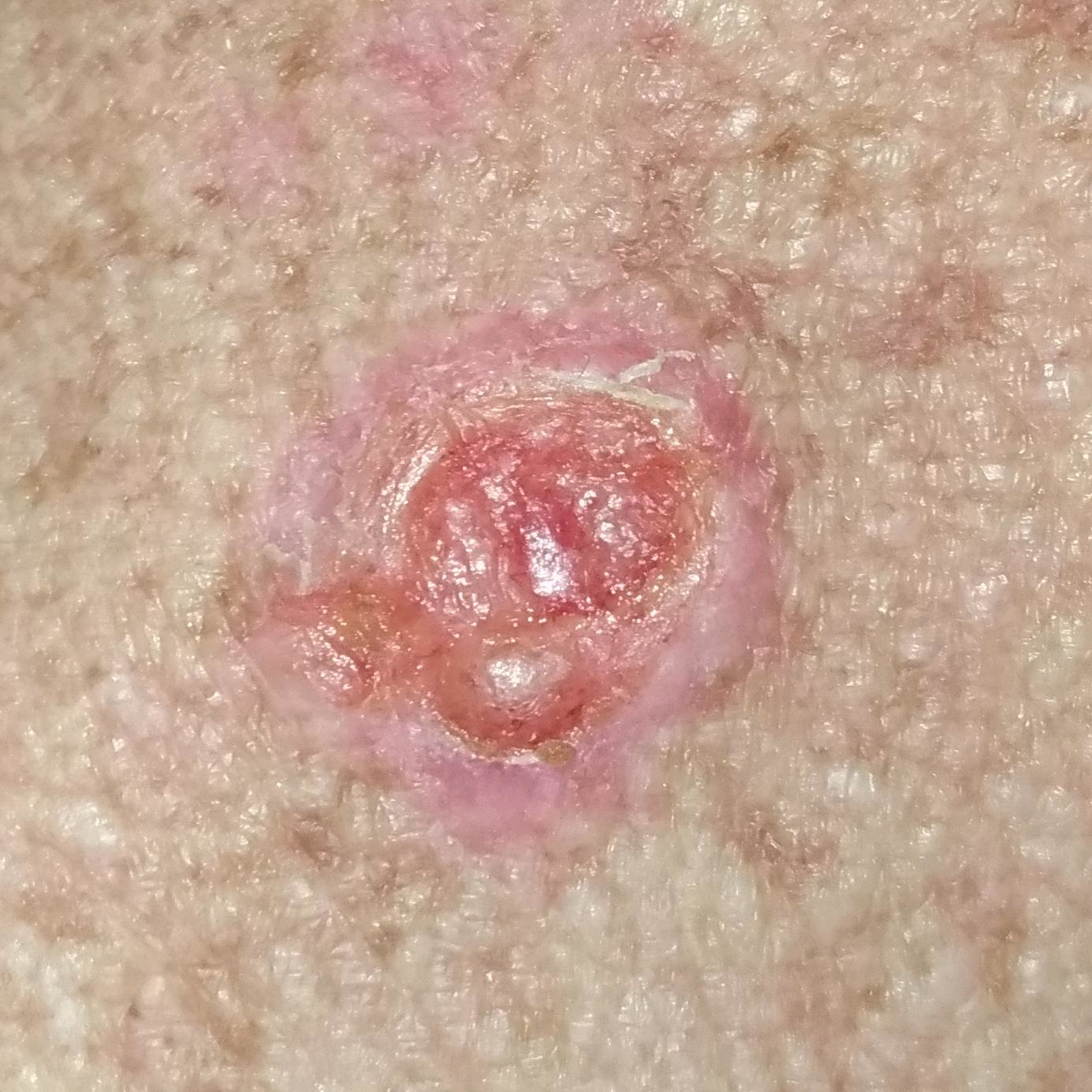Histopathological examination showed a squamous cell carcinoma.